A dermoscopy image of a single skin lesion.
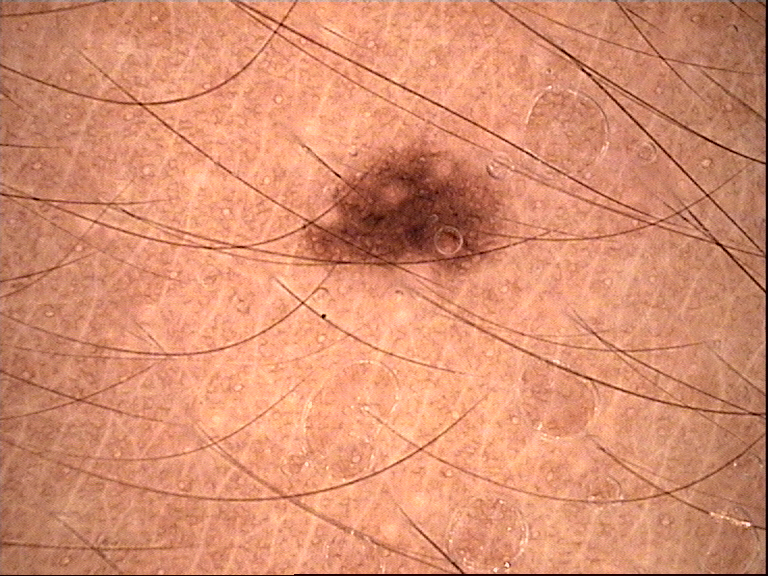Consistent with a benign lesion — a dysplastic junctional nevus.